Texture is reported as flat and rough or flaky; reported lesion symptoms include enlargement and bothersome appearance; reported duration is one to four weeks; the contributor is male; the affected area is the back of the torso and leg; the patient considered this a rash; the photograph is a close-up of the affected area: 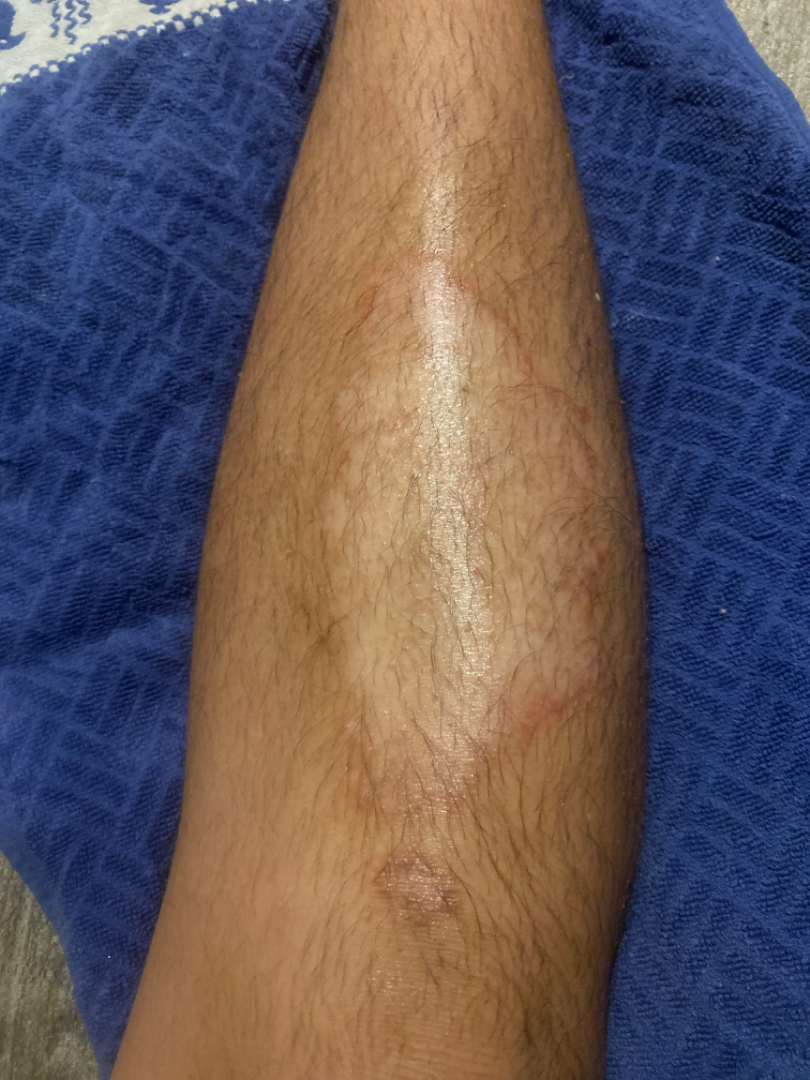Favoring Necrobiosis lipoidica; also consider Tinea; with consideration of Porokeratosis; less likely is Eczema; less probable is Lichen sclerosus.